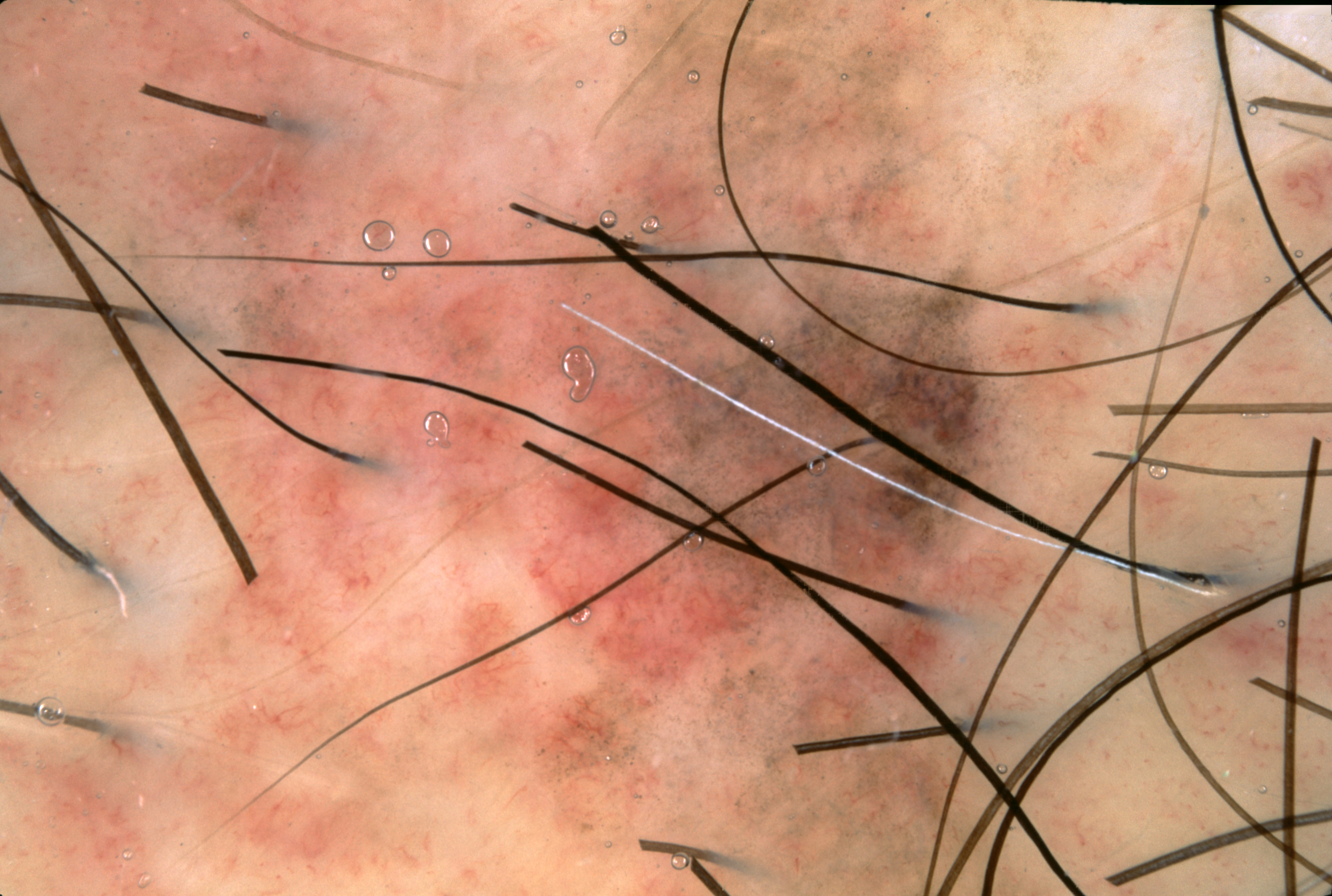<record>
  <patient>
    <sex>male</sex>
    <age_approx>65</age_approx>
  </patient>
  <image>
    <modality>dermoscopy</modality>
  </image>
  <lesion_location>
    <bbox_xyxy>121, 2, 1118, 894</bbox_xyxy>
  </lesion_location>
  <dermoscopic_features>
    <present>pigment network</present>
    <absent>streaks, negative network, milia-like cysts</absent>
  </dermoscopic_features>
  <diagnosis>
    <name>melanoma</name>
    <malignancy>malignant</malignancy>
    <lineage>melanocytic</lineage>
    <provenance>histopathology</provenance>
  </diagnosis>
</record>